The affected area is the leg · the patient considered this a growth or mole · FST III; non-clinician graders estimated MST 1 (US pool) or 2 (India pool) · the lesion is described as rough or flaky, flat, fluid-filled and raised or bumpy · this image was taken at a distance · symptoms reported: darkening, bothersome appearance, pain, bleeding, burning, enlargement and itching — 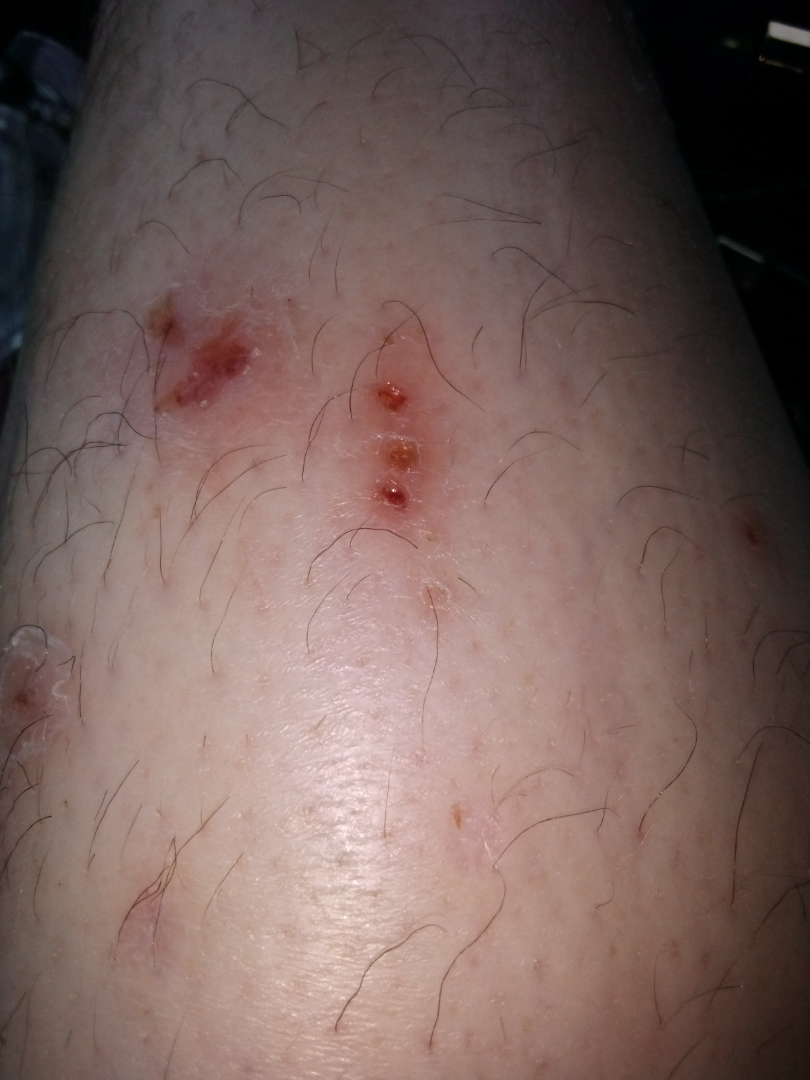Findings:
- assessment — unable to determine